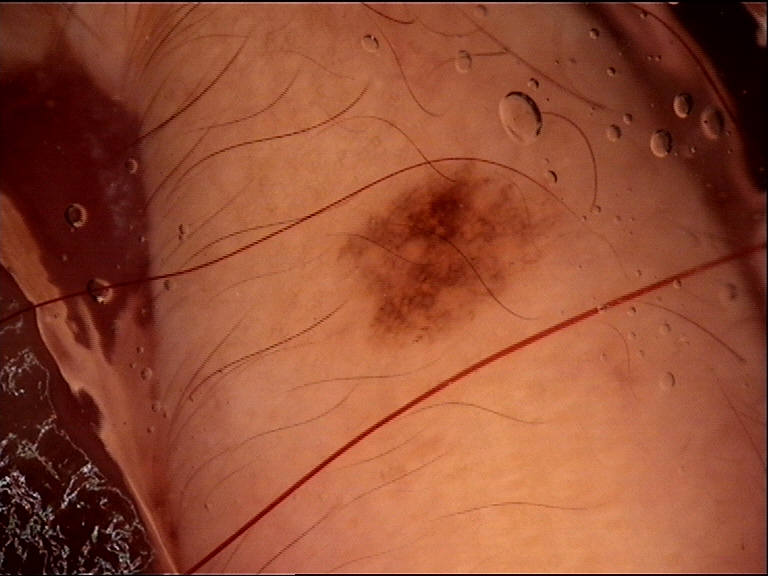Labeled as a dysplastic junctional nevus.